No relevant systemic symptoms. Located on the arm. A close-up photograph. The patient considered this a rash. Symptoms reported: itching and burning. The contributor notes the condition has been present for about one day. The contributor notes the lesion is flat: 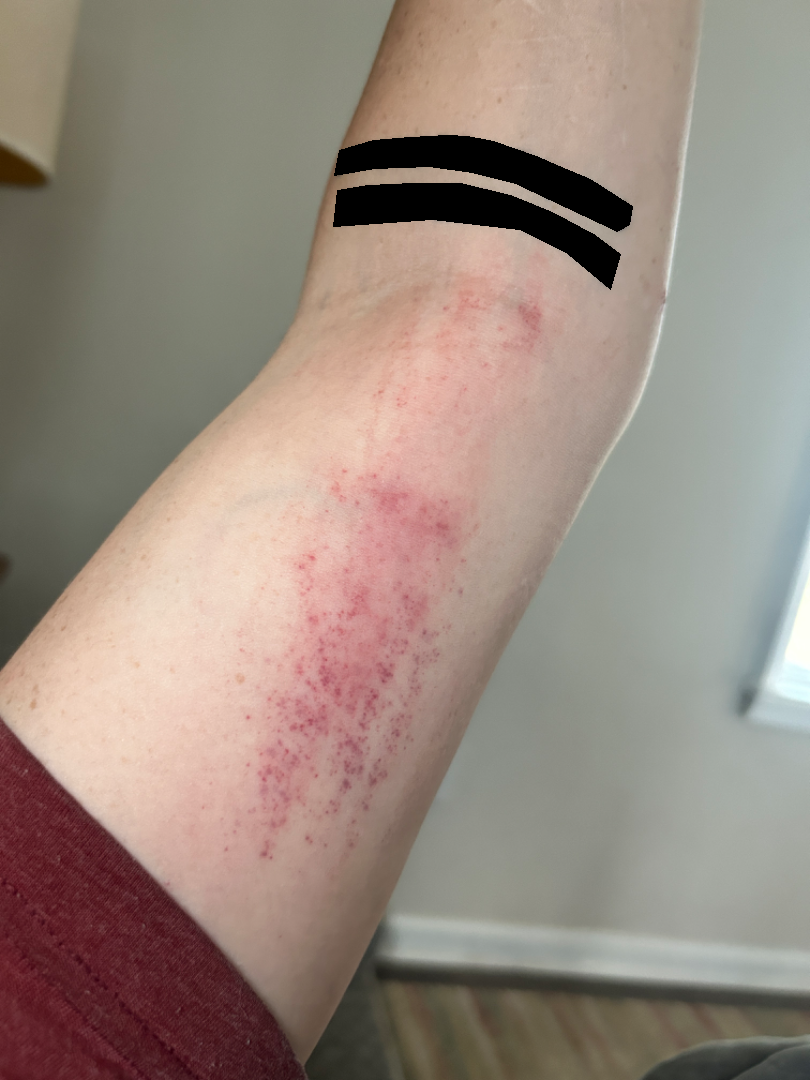Impression:
On photographic review by a dermatologist: consistent with ecchymoses.